Male patient, age 30–39 · the arm is involved · an image taken at an angle.
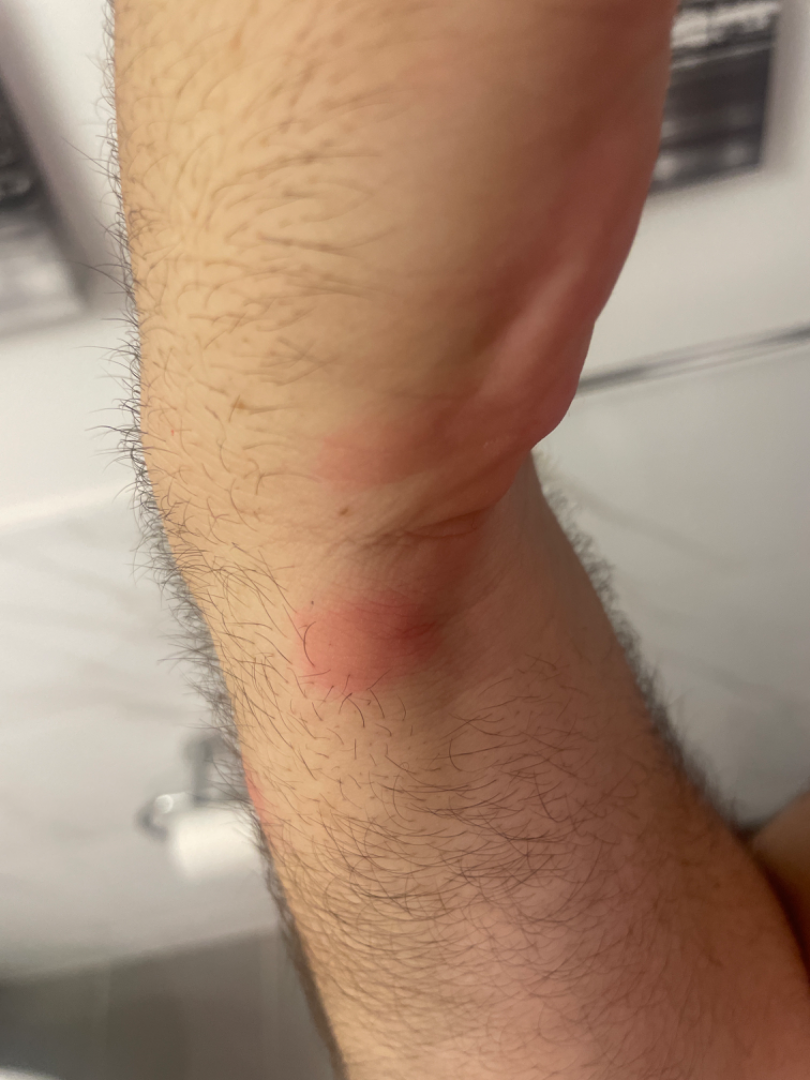The case was difficult to assess from the available photograph.